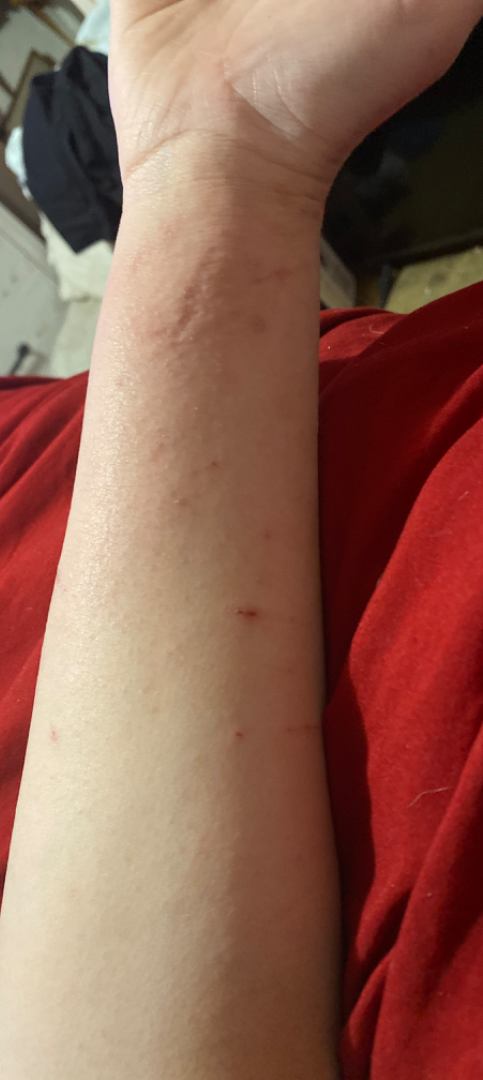No associated systemic symptoms reported. The photograph was taken at a distance. The condition has been present for less than one week. The lesion is described as raised or bumpy. Female subject, age 18–29. The lesion involves the back of the hand and arm. Eczema (0.67); Allergic Contact Dermatitis (0.33).